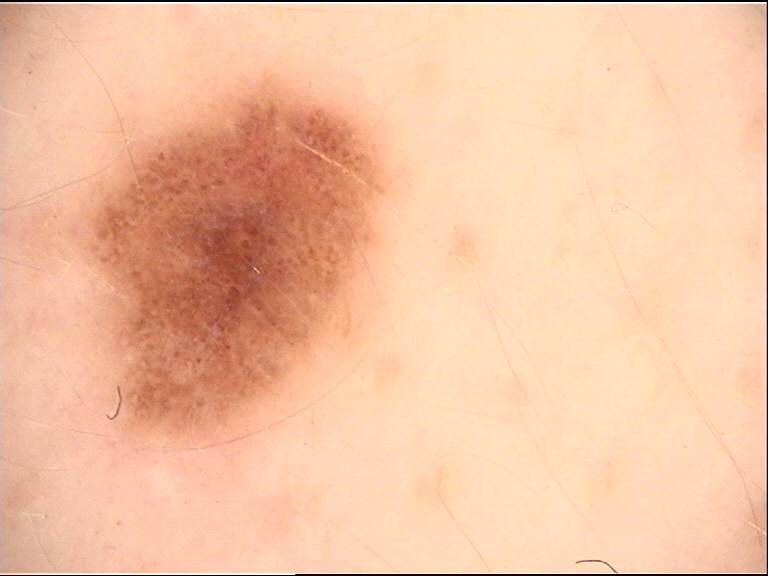Consistent with a dysplastic compound nevus.